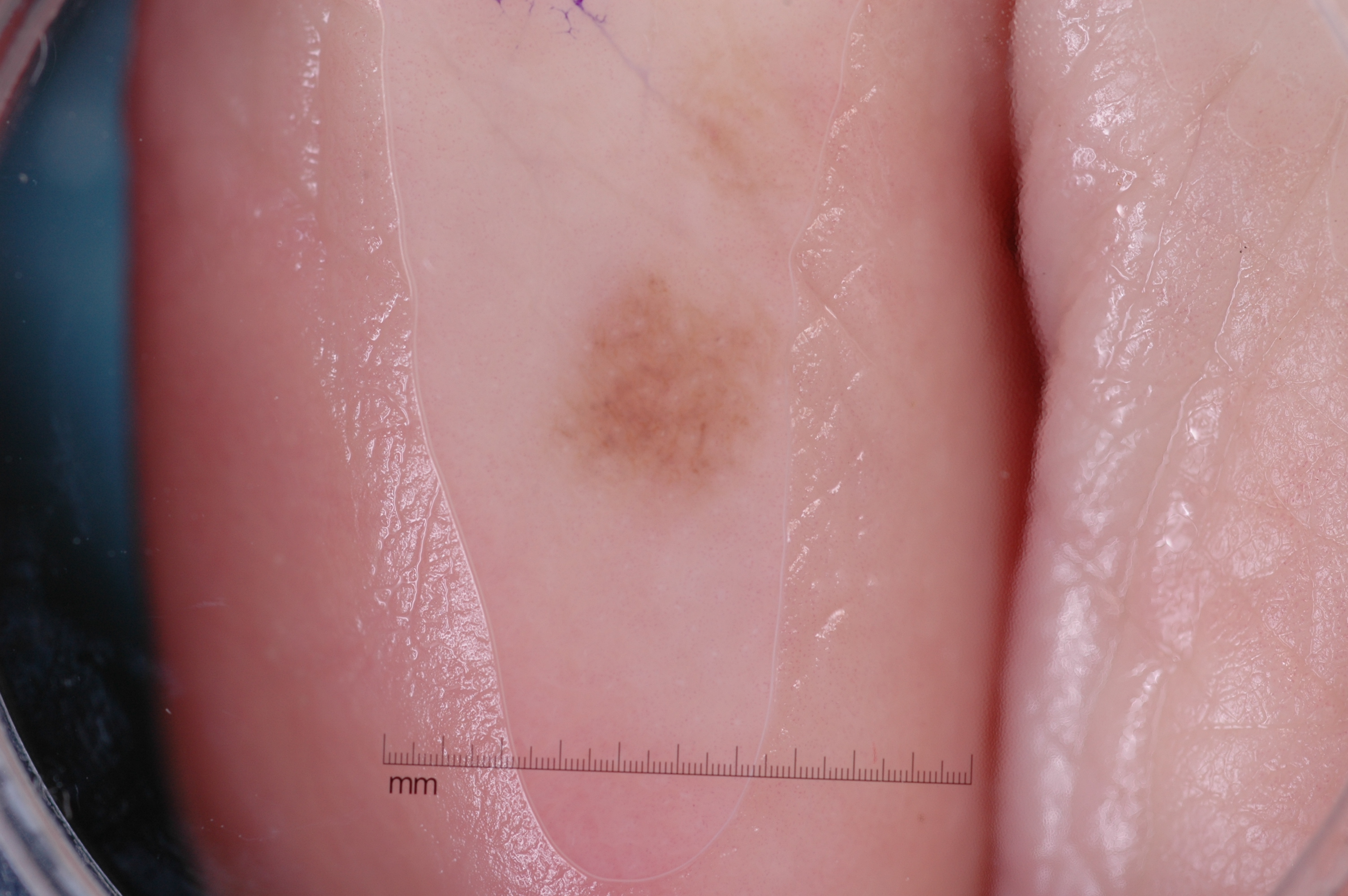A dermoscopic view of a skin lesion.
The subject is a male in their 60s.
As (left, top, right, bottom), the lesion is bounded by box(549, 269, 777, 507).
On dermoscopy, the lesion shows no negative network, pigment network, milia-like cysts, or streaks.
Expert review diagnosed this as a melanocytic nevus.